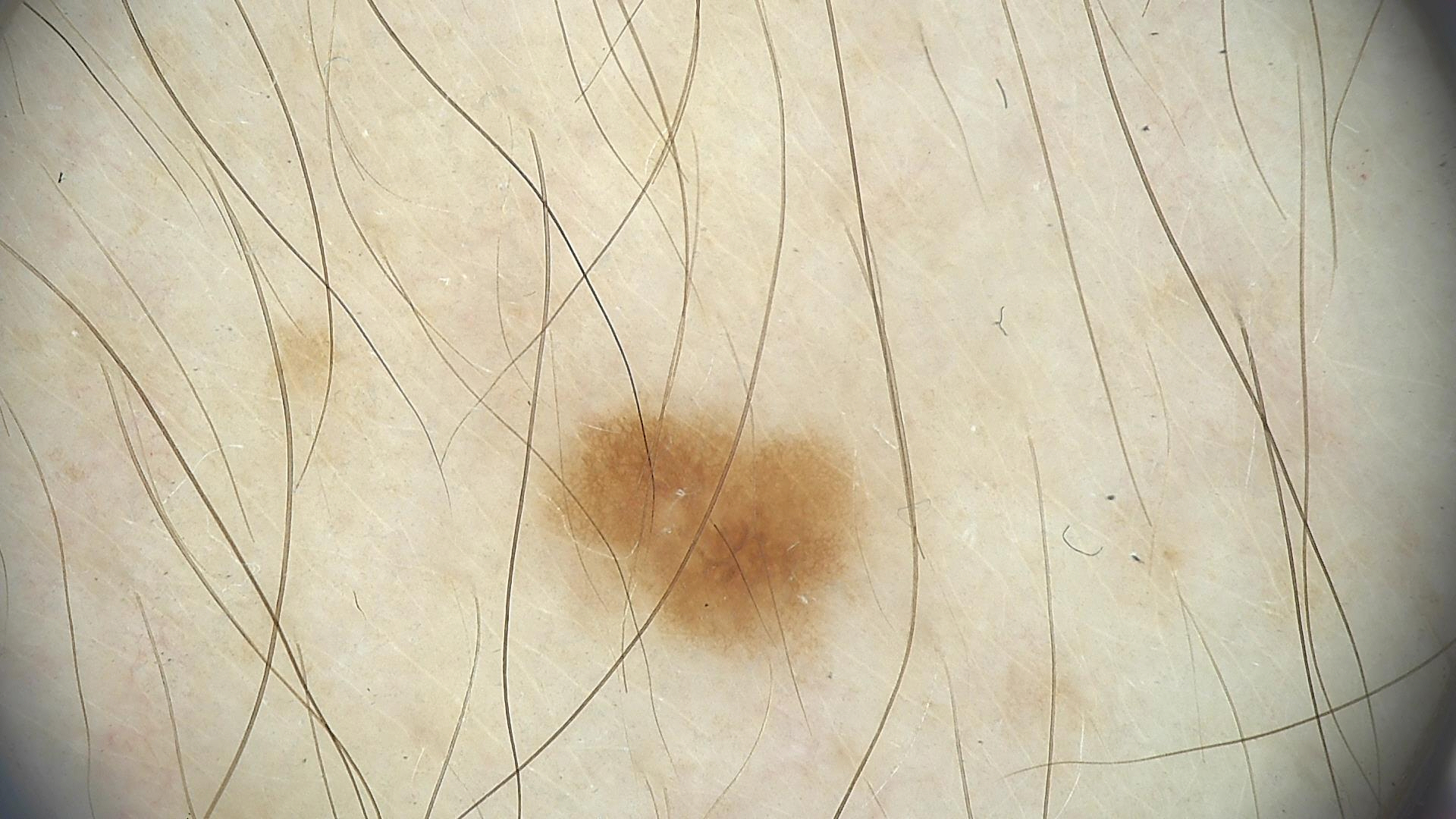Q: What is the imaging modality?
A: dermatoscopy
Q: What is this lesion?
A: dysplastic junctional nevus (expert consensus)